The patient is a female aged 18–29 · this is a close-up image · located on the leg: 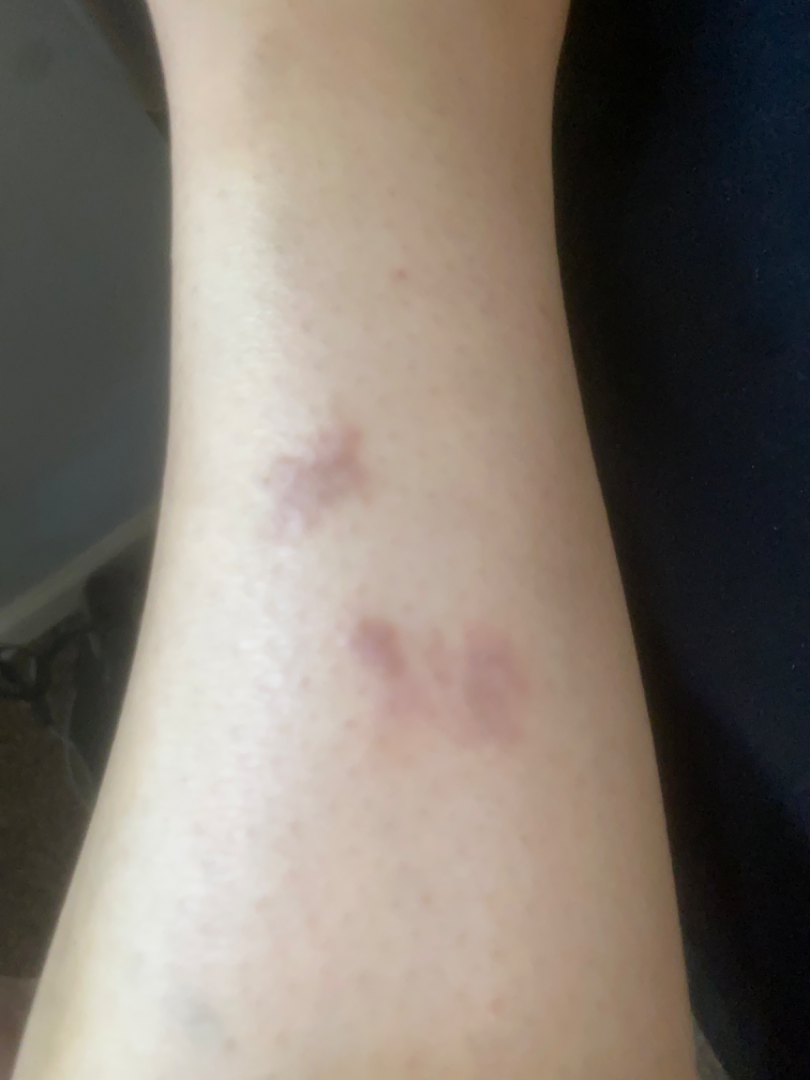| feature | finding |
|---|---|
| assessment | not assessable |
| other reported symptoms | none reported |
| present for | three to twelve months |
| texture | rough or flaky and raised or bumpy |
| patient describes the issue as | a rash |